Close-up view · the affected area is the leg:
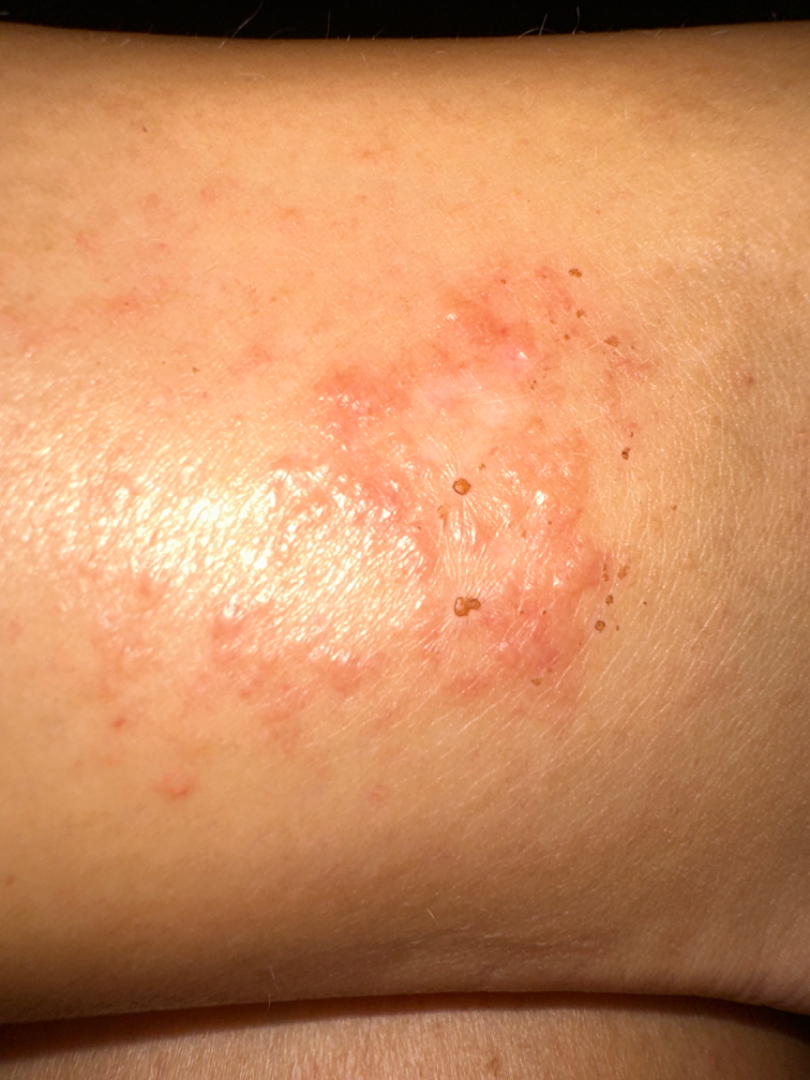Present for less than one week.
The lesion is described as raised or bumpy.
Self-categorized by the patient as a rash.
The reviewer's impression was Eczema.